The front of the torso is involved; this is a close-up image.
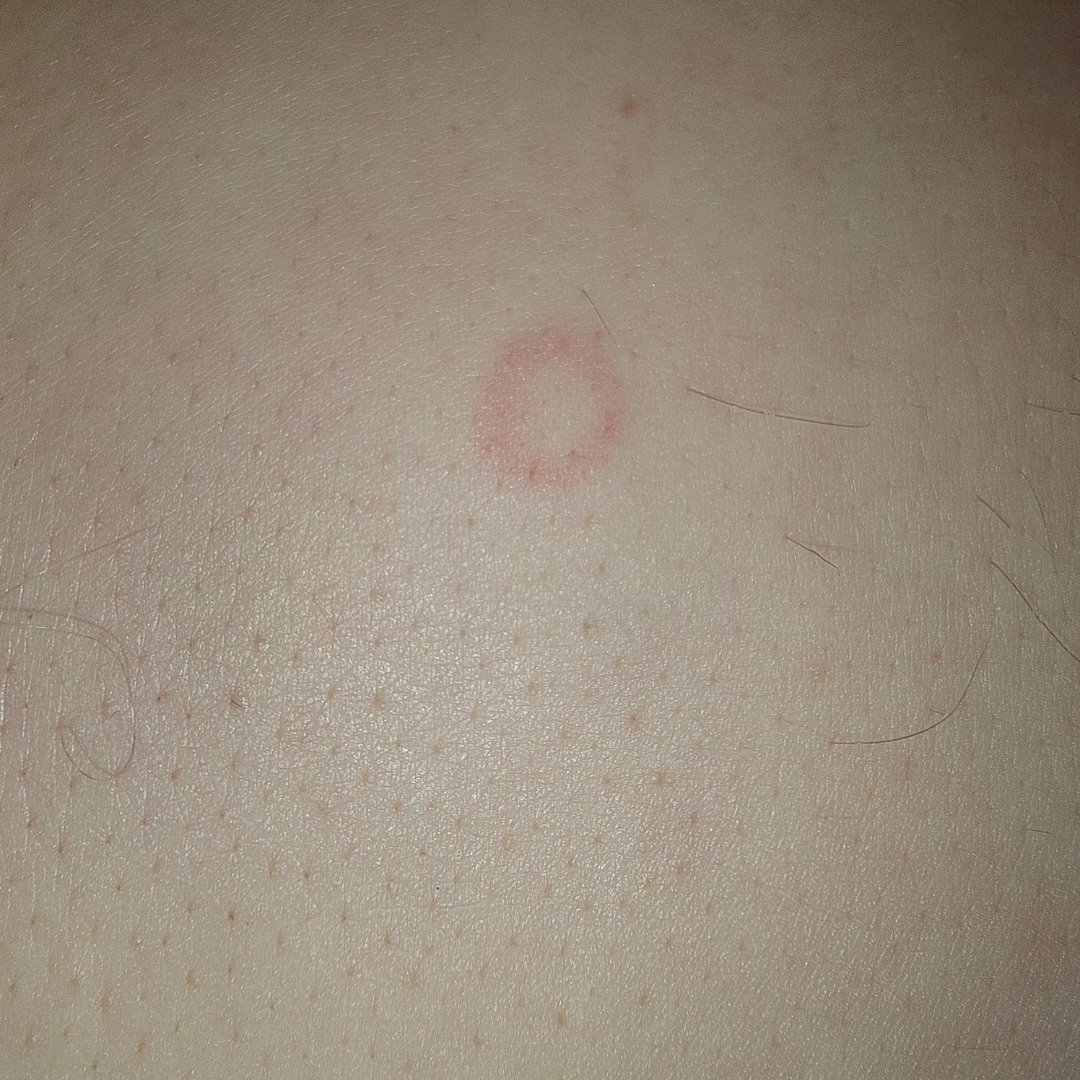On teledermatology review: the primary impression is Annular erythema; also raised was Granuloma annulare; a remote consideration is Tinea.